A patient in their 70s · a clinical photograph showing a skin lesion: 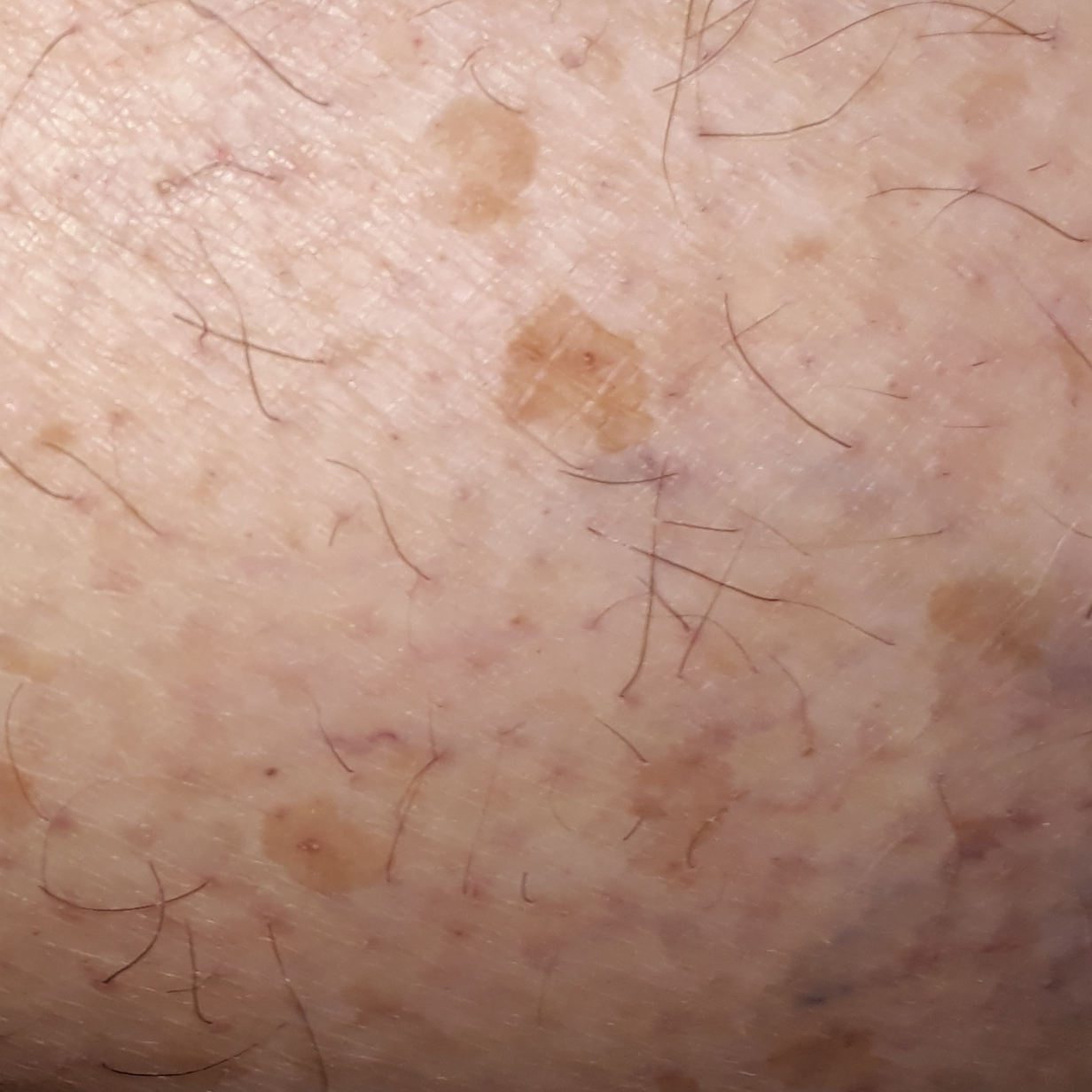Located on an arm.
The patient reports that the lesion is elevated, itches, and has grown, but has not changed and has not bled.
Expert review favored a benign skin lesion — a seborrheic keratosis.